Reported duration is one to four weeks, the photograph was taken at an angle, self-categorized by the patient as a rash, located on the arm and back of the torso, the contributor notes itching, the lesion is described as raised or bumpy: 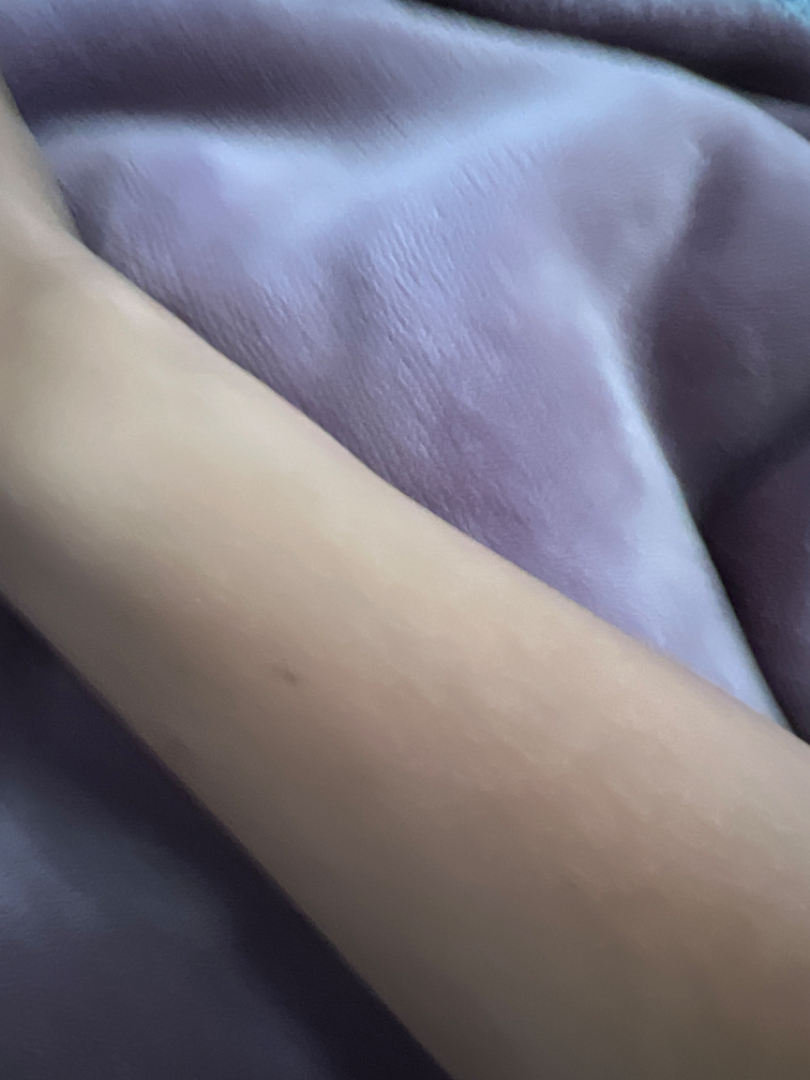The case was indeterminate on photographic review.